A male patient aged 78-82 · the patient is Fitzpatrick skin type II.
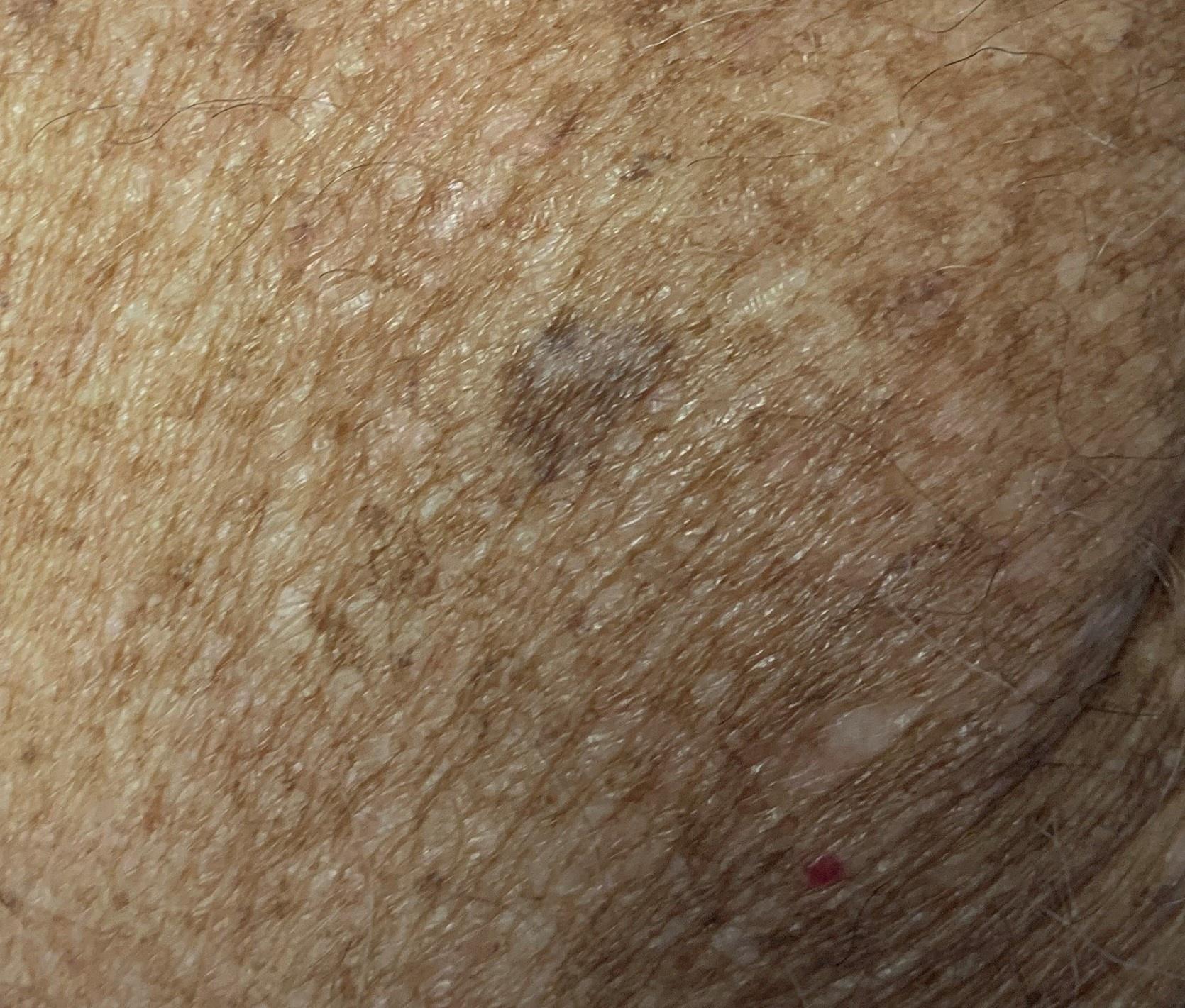The lesion involves the posterior trunk.
The clinical impression was a lichen planus like keratosis.